A dermoscopic image of a skin lesion.
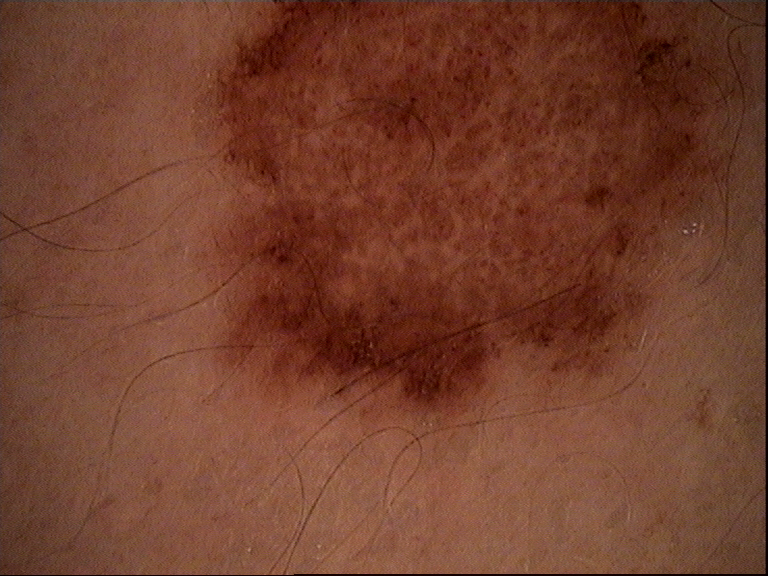Labeled as a benign lesion — a dysplastic junctional nevus.